The lesion is described as flat · the patient described the issue as a growth or mole · the lesion is associated with itching · a close-up photograph · located on the leg · the contributor is 18–29, female · no relevant systemic symptoms · present for less than one week.
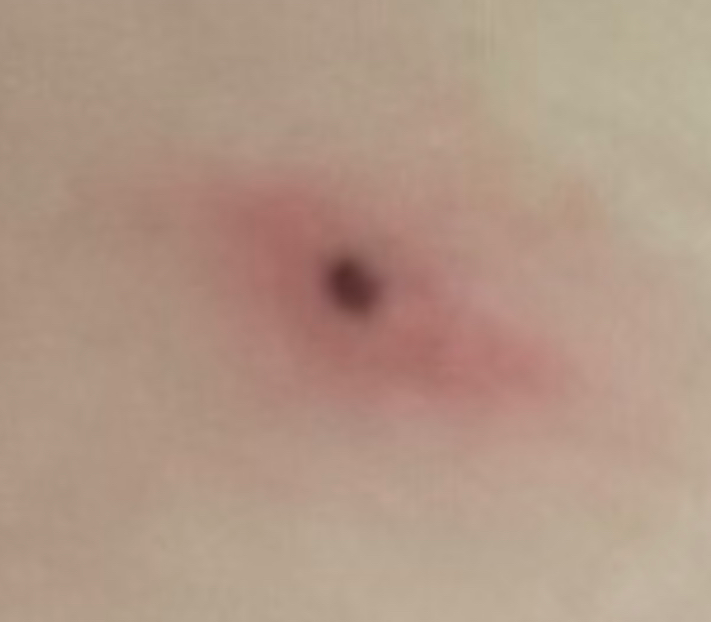Review: The dermatologist could not determine a likely condition from the photograph alone.